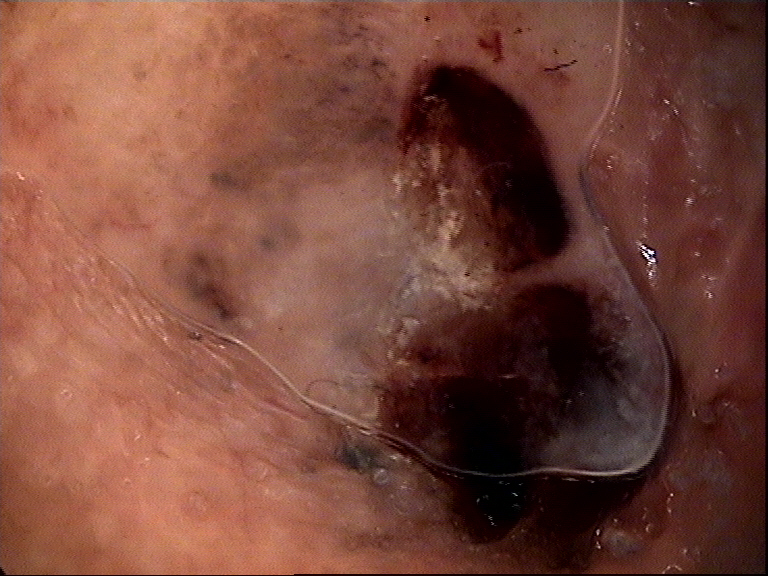• imaging · dermoscopy
• label · basal cell carcinoma (biopsy-proven)